The front of the torso is involved, the photograph is a close-up of the affected area: 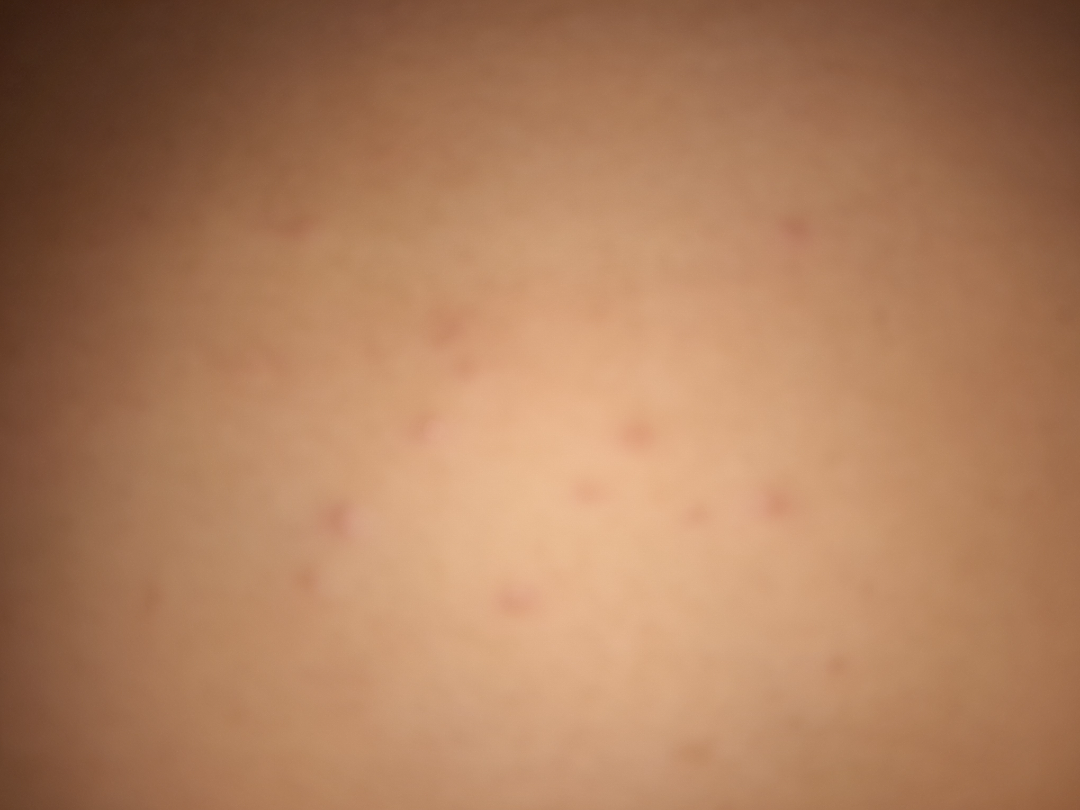lesion symptoms = itching and bothersome appearance | self-categorized as = a rash | present for = less than one week | other reported symptoms = fatigue, joint pain and chills | surface texture = raised or bumpy and fluid-filled | skin tone = Fitzpatrick II; lay reviewers estimated a Monk Skin Tone of 4 | dermatologist impression = the differential includes Folliculitis and Molluscum Contagiosum, with no clear leading consideration; less probable is Scabies.